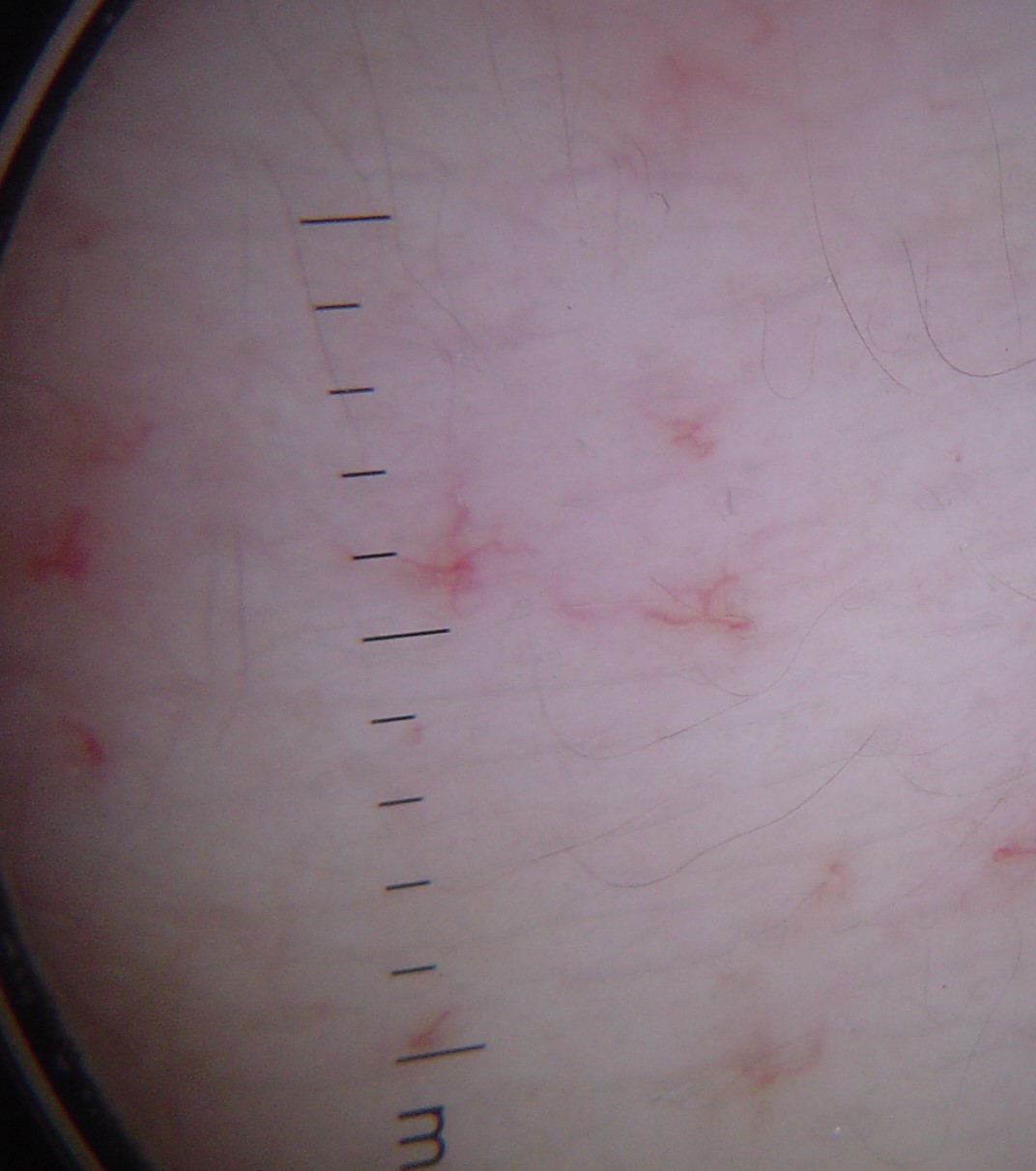imaging = dermatoscopy; class = spider angioma (expert consensus).